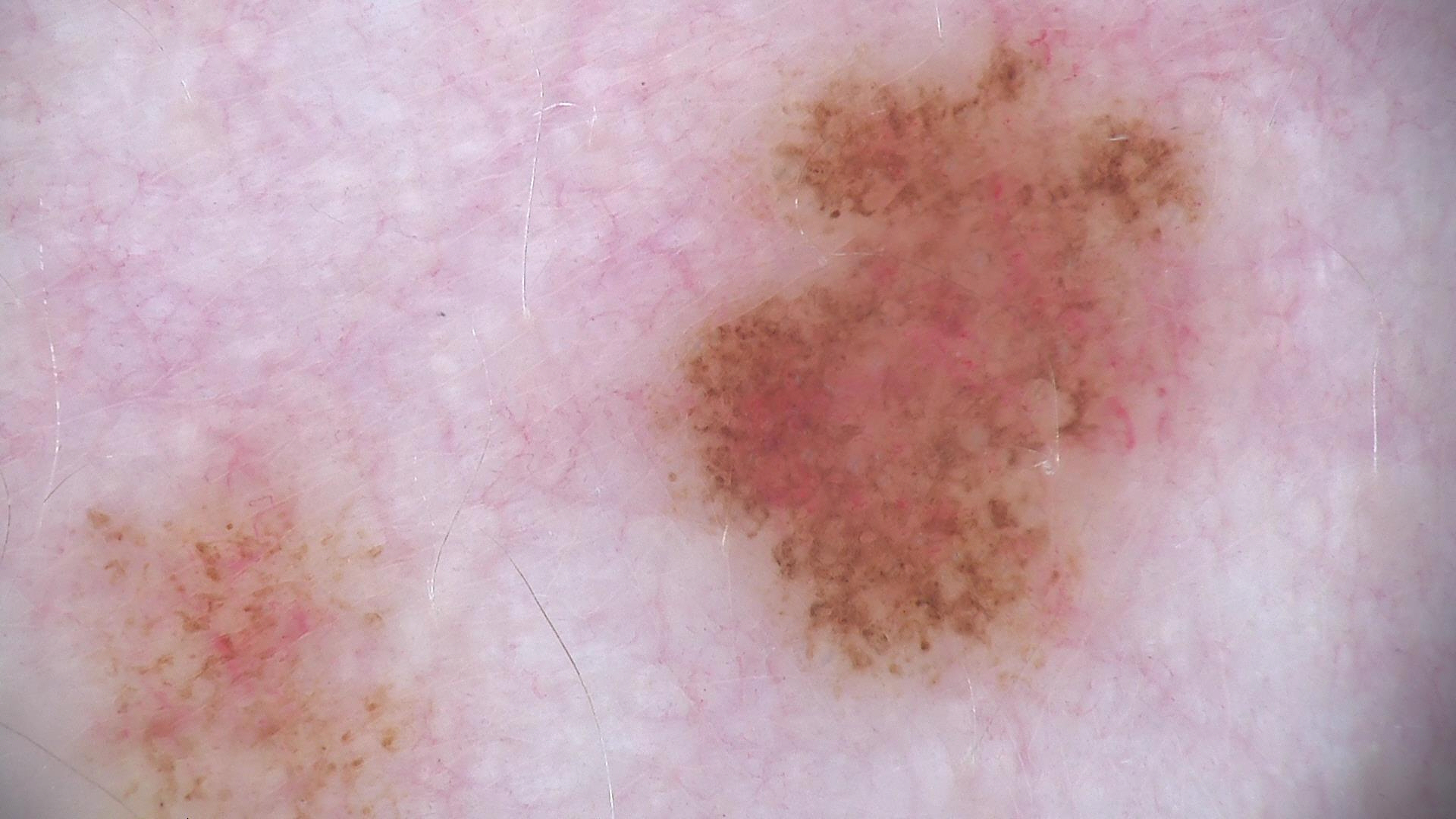Case:
Dermoscopy of a skin lesion.
Conclusion:
Consistent with a benign lesion — a dysplastic junctional nevus.